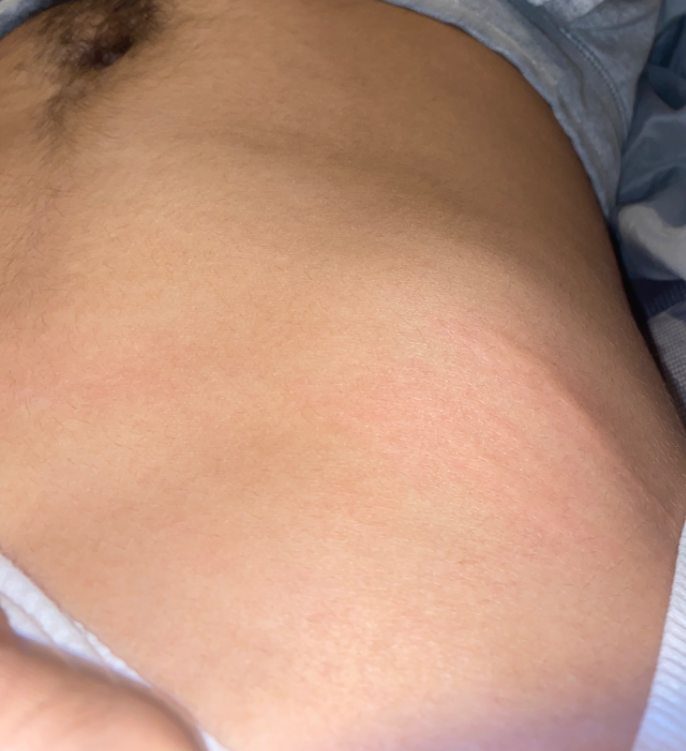Background:
Located on the front of the torso. The contributor is male. The photo was captured at an angle.
Findings:
The reviewing panel's impression was: favoring Urticaria; an alternative is Allergic Contact Dermatitis; less likely is Insect Bite.